A female patient aged approximately 70 · a dermoscopic image of a skin lesion.
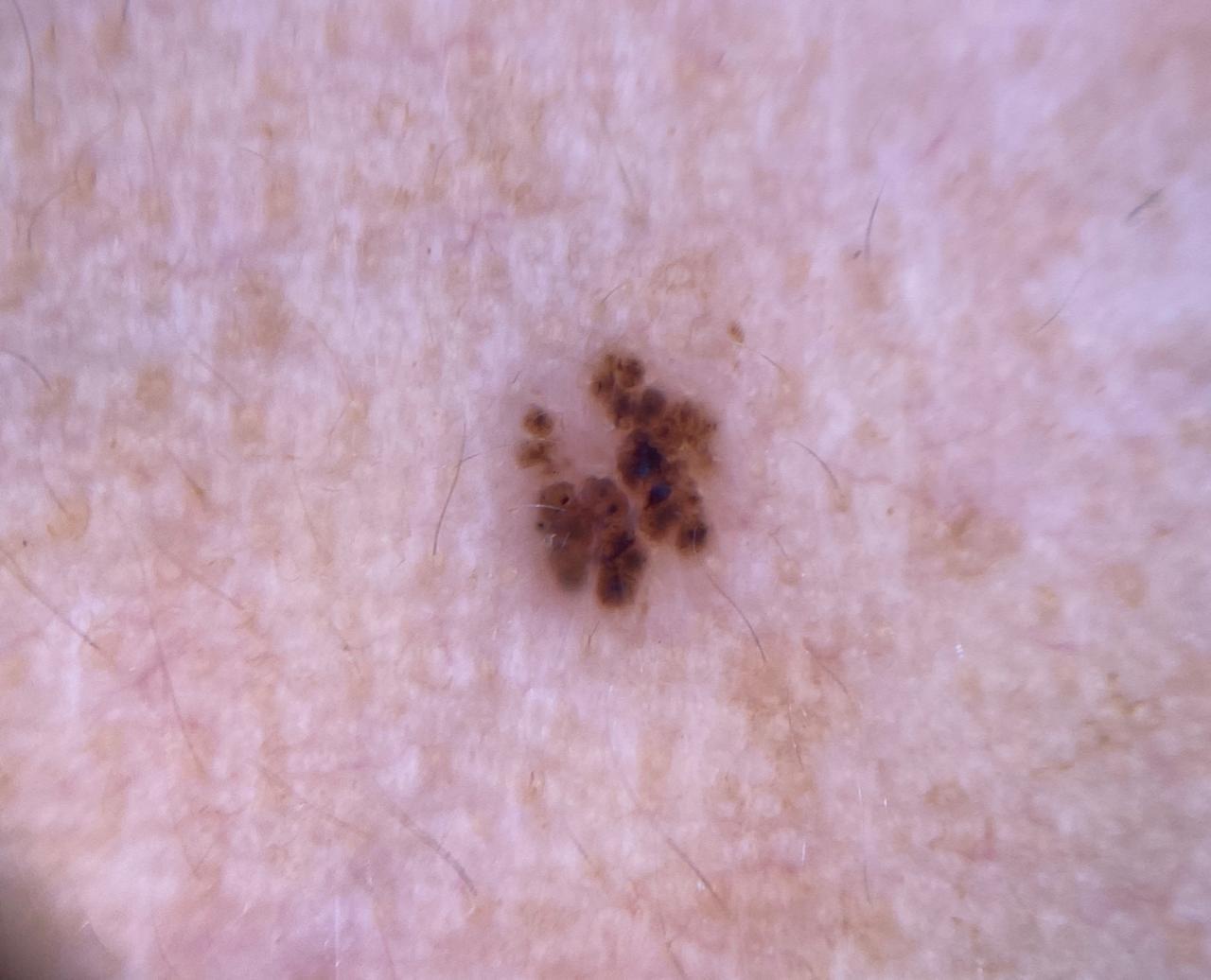Summary:
The lesion involves the head or neck.
Conclusion:
Biopsy-confirmed as a basal cell carcinoma.